Dermoscopy of a skin lesion.
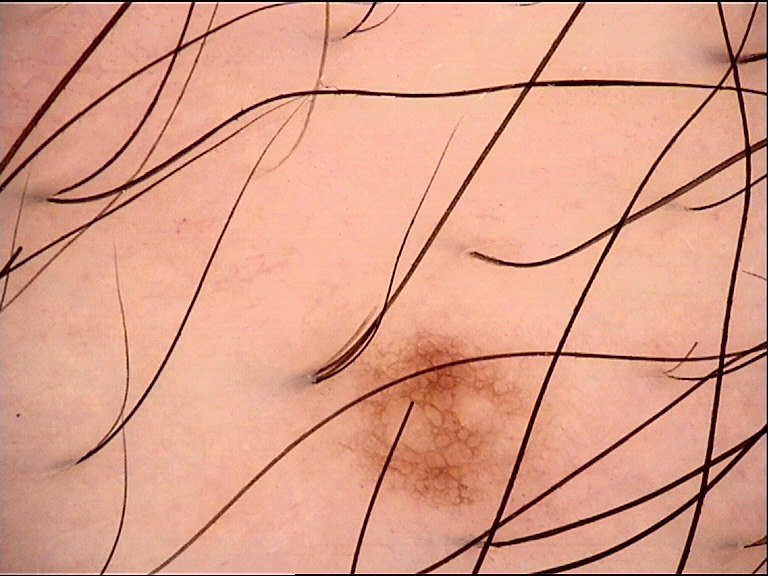Conclusion: Consistent with a dysplastic junctional nevus.